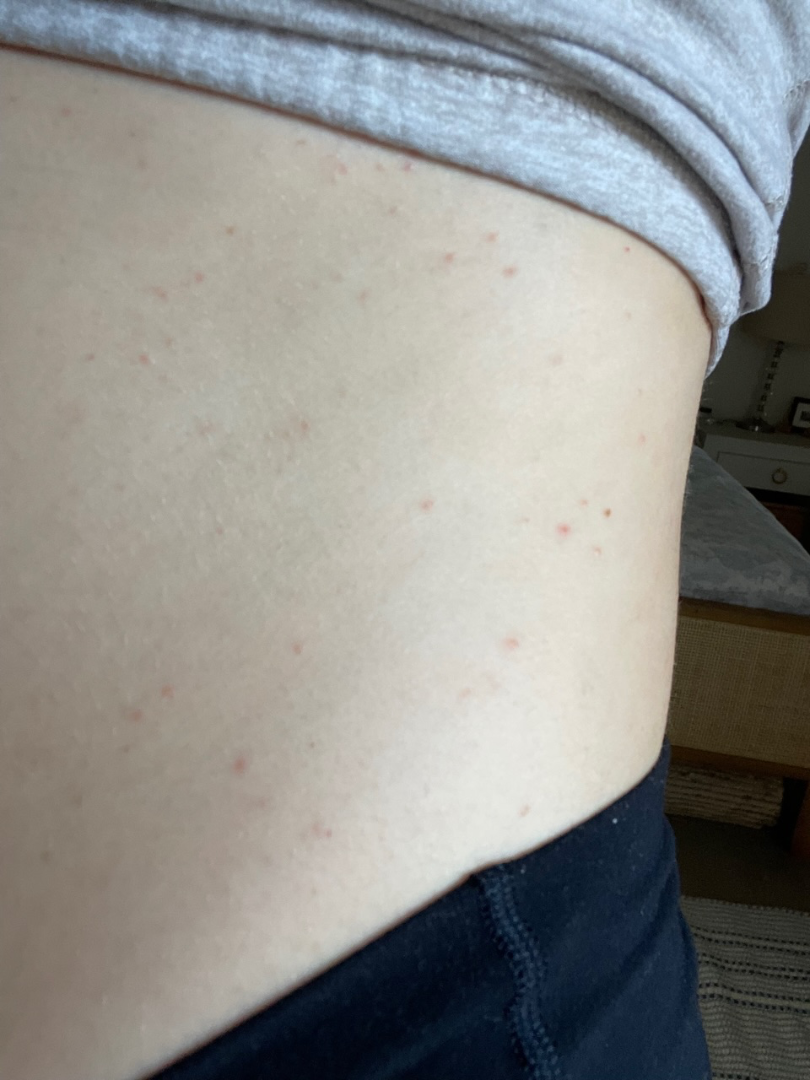assessment=ungradable on photographic review | patient describes the issue as=a rash | location=front of the torso, head or neck and arm | framing=at an angle | reported symptoms=enlargement, bothersome appearance and itching | described texture=raised or bumpy.